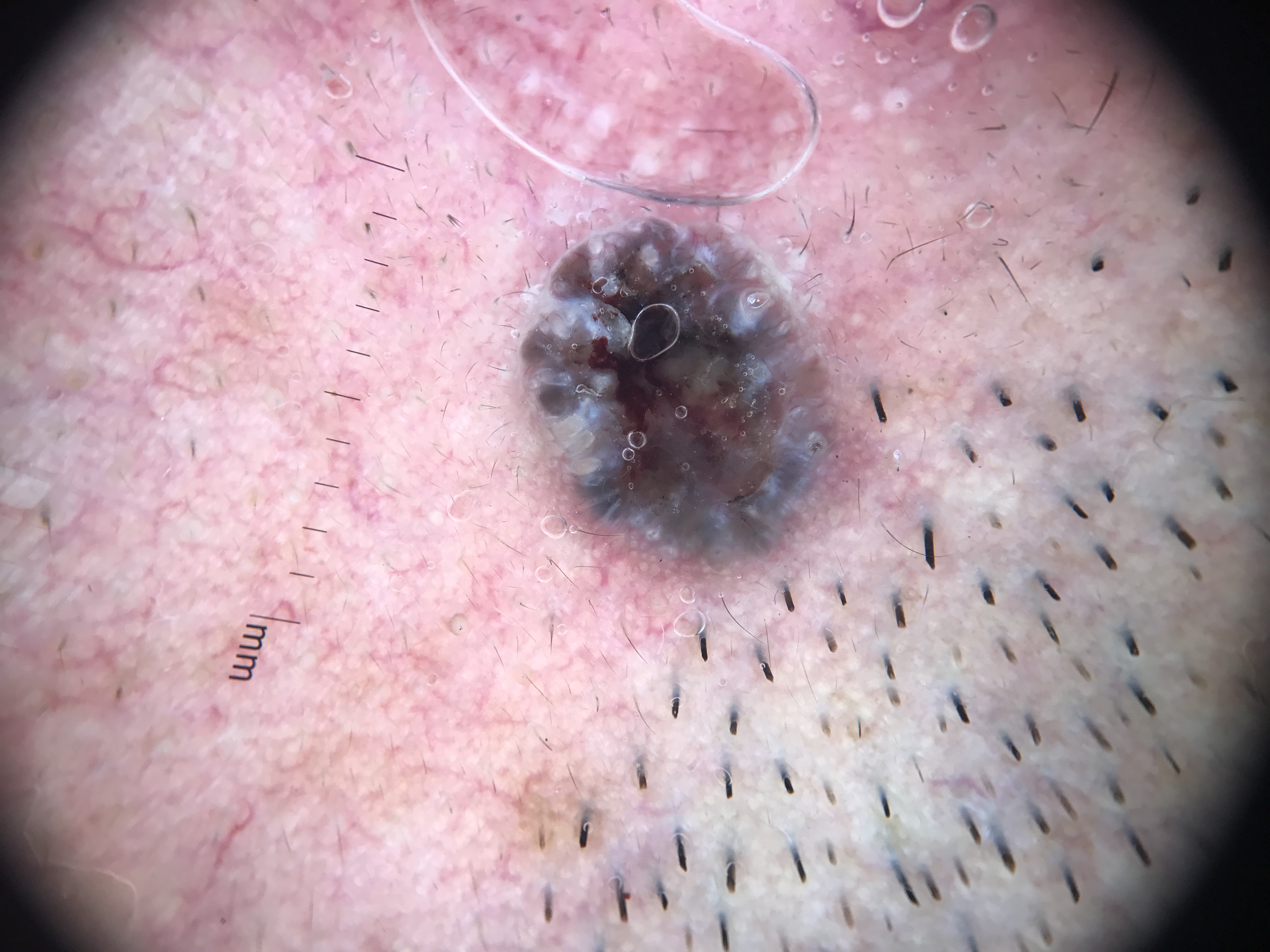The biopsy diagnosis was a basal cell carcinoma.